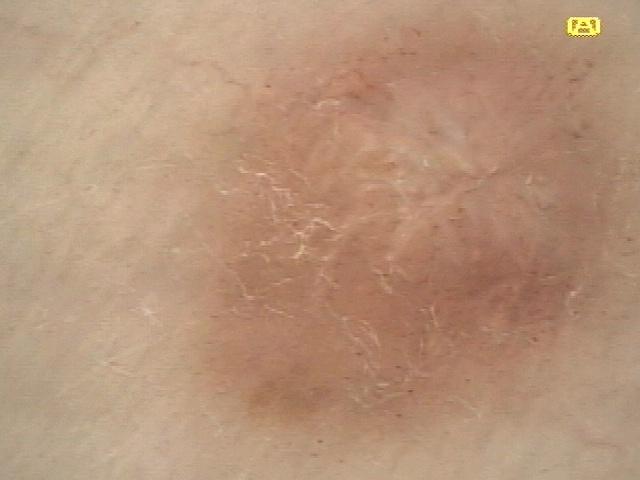A contact-polarized dermoscopy image of a skin lesion. Recorded as skin type II. A female patient about 80 years old. The lesion is located on a lower extremity. Expert review favored a dermatofibroma.